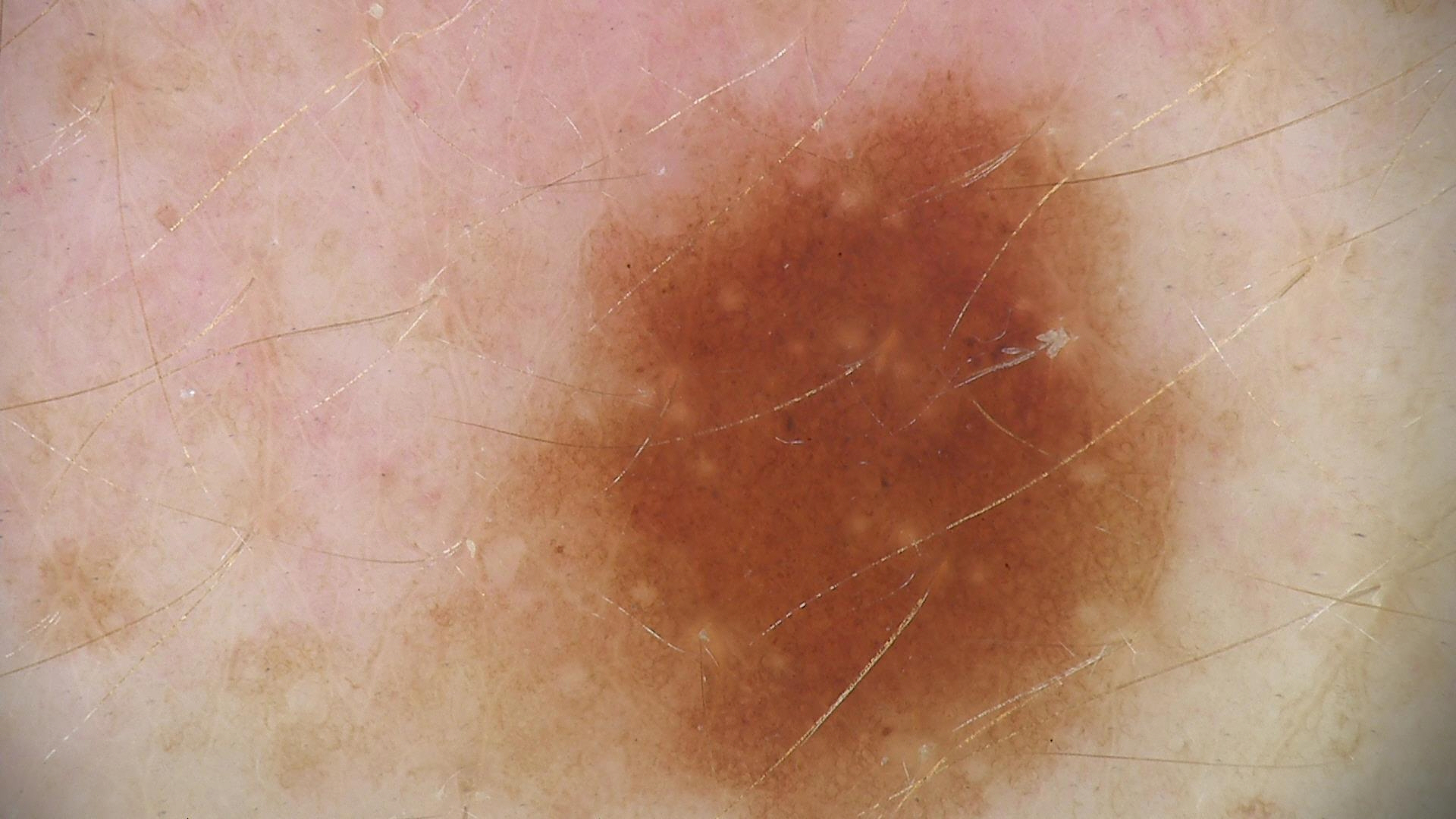Diagnosed as a dysplastic junctional nevus.